The photo was captured at an angle; skin tone: Fitzpatrick skin type II: 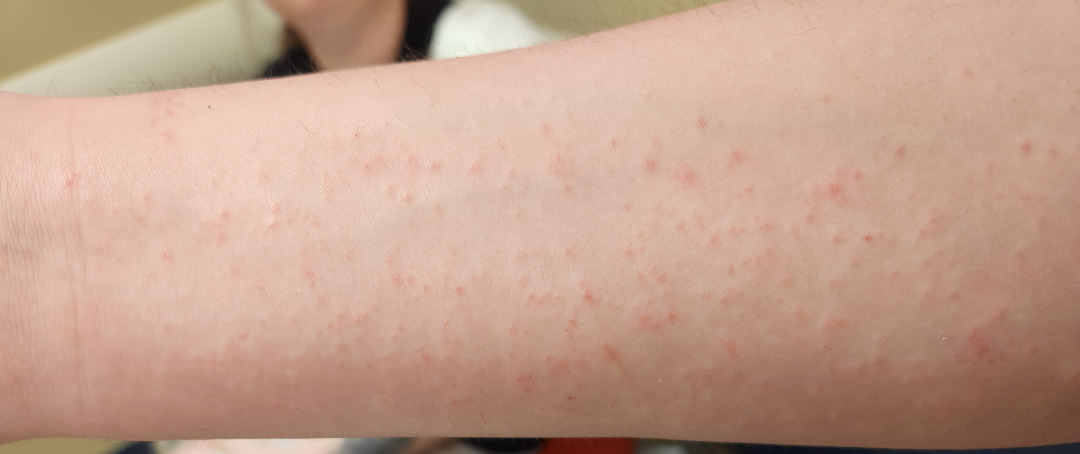Case summary:
- impression — most consistent with Allergic Contact Dermatitis; also raised was Folliculitis; with consideration of Insect Bite